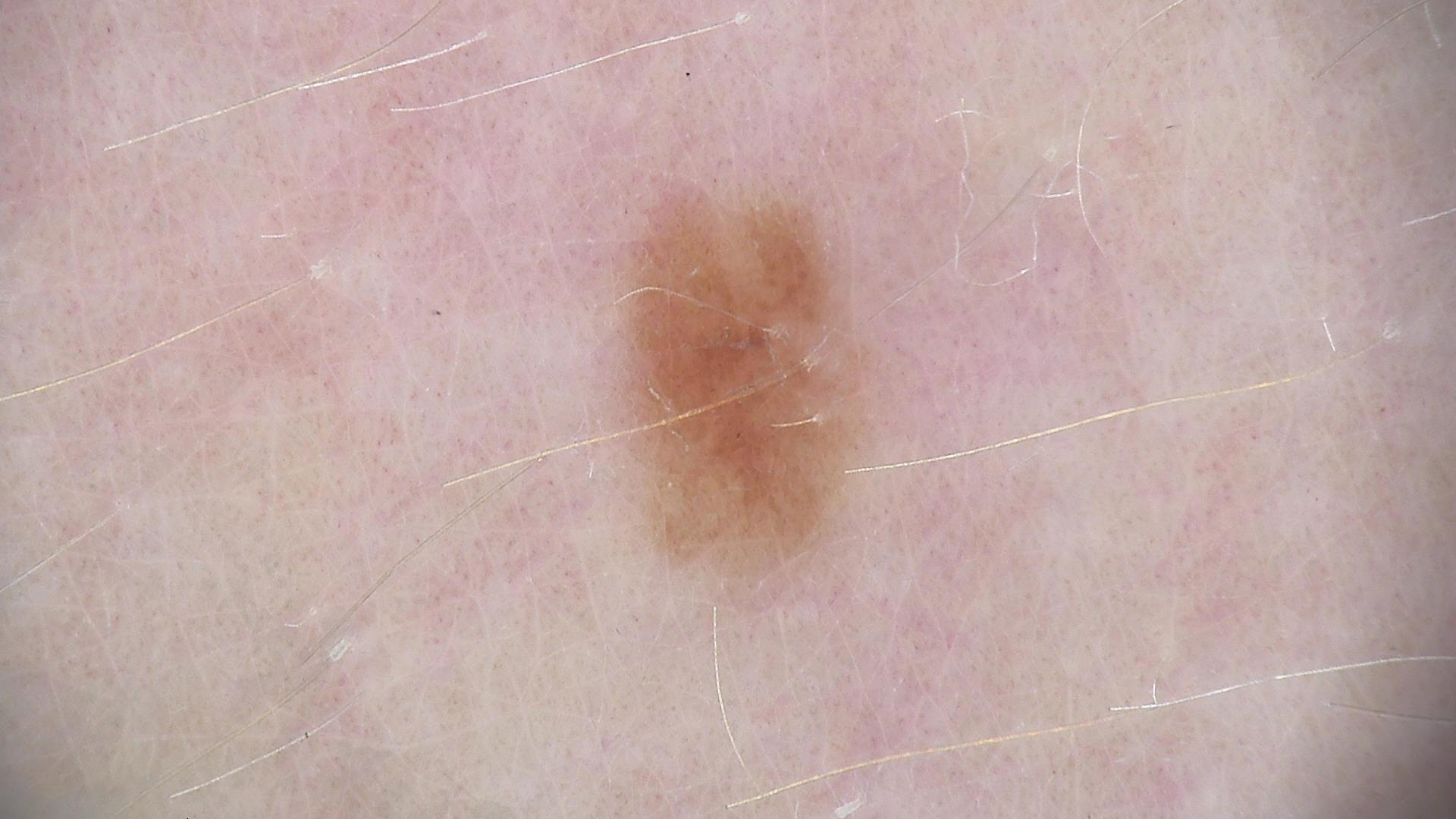| field | value |
|---|---|
| modality | dermatoscopy |
| assessment | dysplastic junctional nevus (expert consensus) |